A clinical photo of a skin lesion taken with a smartphone; the chart notes prior skin cancer (patient or family), prior malignancy (patient or family), and no pesticide exposure; the patient was assessed as skin type III; a female patient in their mid-60s — 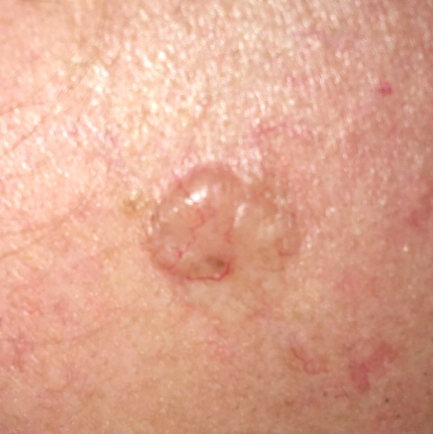Patient and lesion:
The lesion is on the face. The lesion measures approximately 9 × 6 mm.
Conclusion:
Biopsy-confirmed as a basal cell carcinoma.